A female patient in their mid-30s. The chart records no previous melanoma and no first-degree relative with melanoma. The patient was assessed as Fitzpatrick skin type II. A dermoscopy image of a single skin lesion.
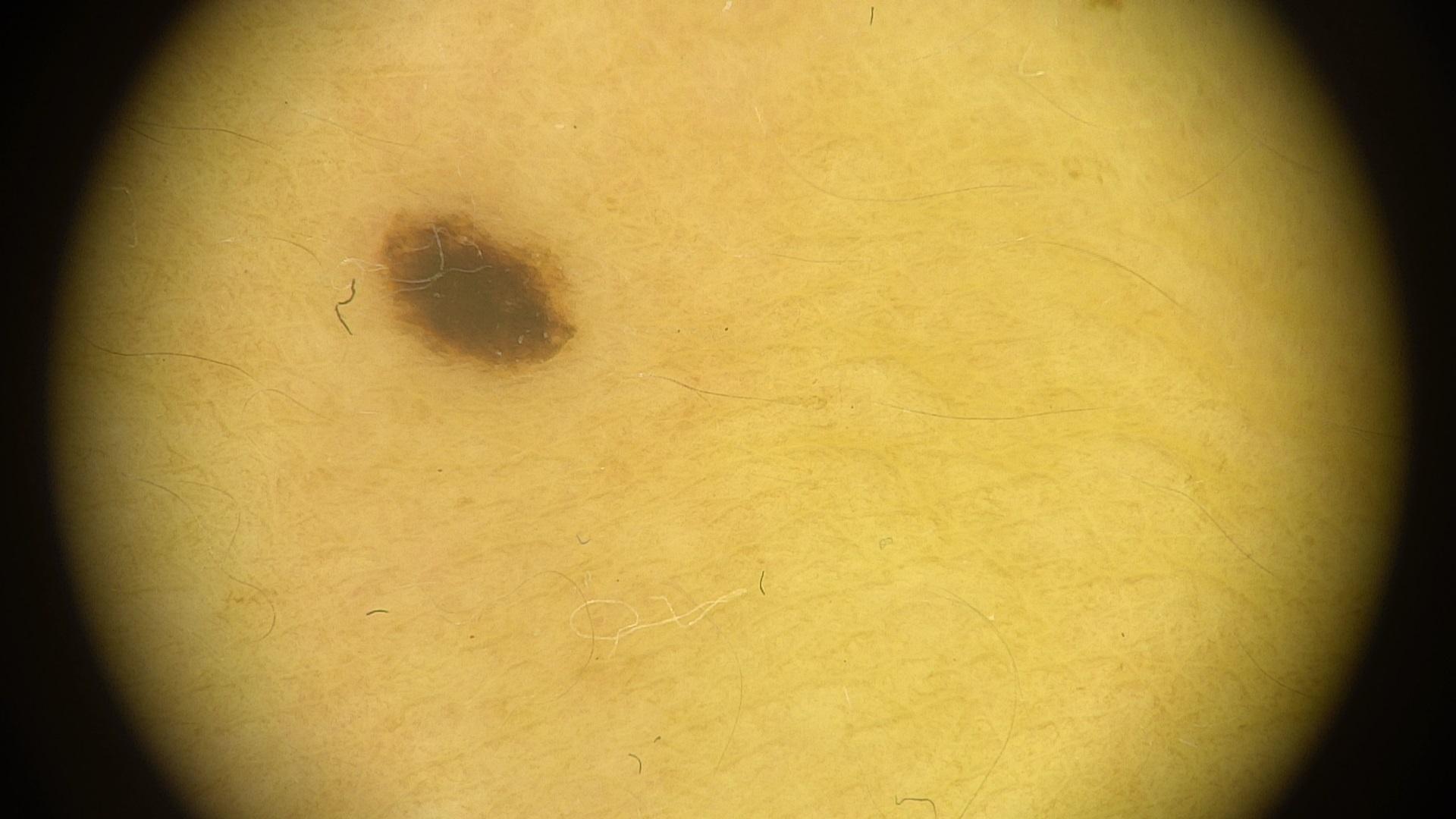Clinical context:
The lesion is located on the trunk.
Assessment:
Expert review favored a nevus.